Present for three to twelve months, reported lesion symptoms include bothersome appearance, located on the arm, the lesion is described as rough or flaky, the photo was captured at a distance, Fitzpatrick III; non-clinician graders estimated MST 2 or 3 (two reviewer pools): 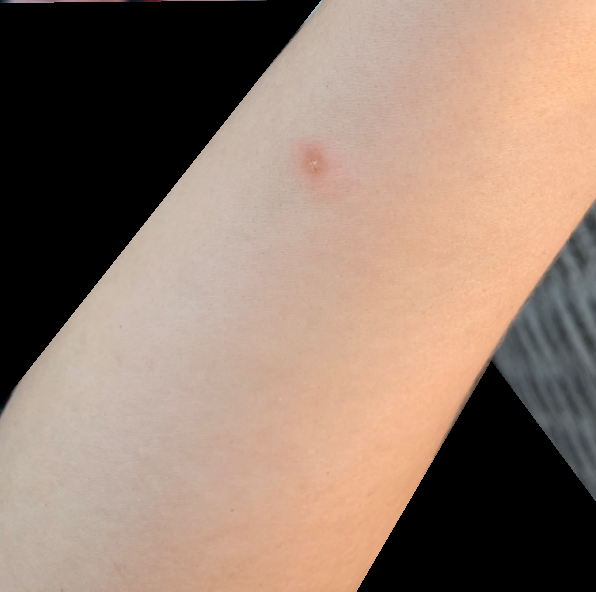assessment: unable to determine.